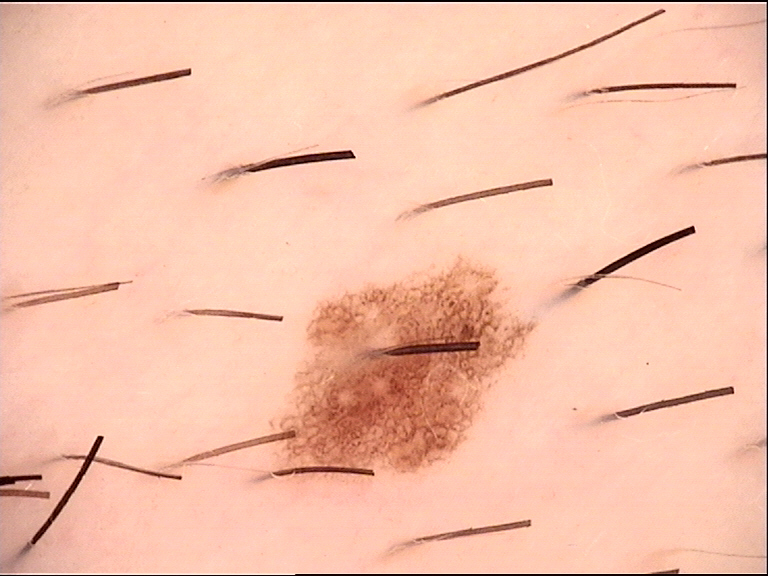imaging = dermatoscopy
diagnostic label = dysplastic junctional nevus (expert consensus)